This is a dermoscopic photograph of a skin lesion. A female subject in their 60s: 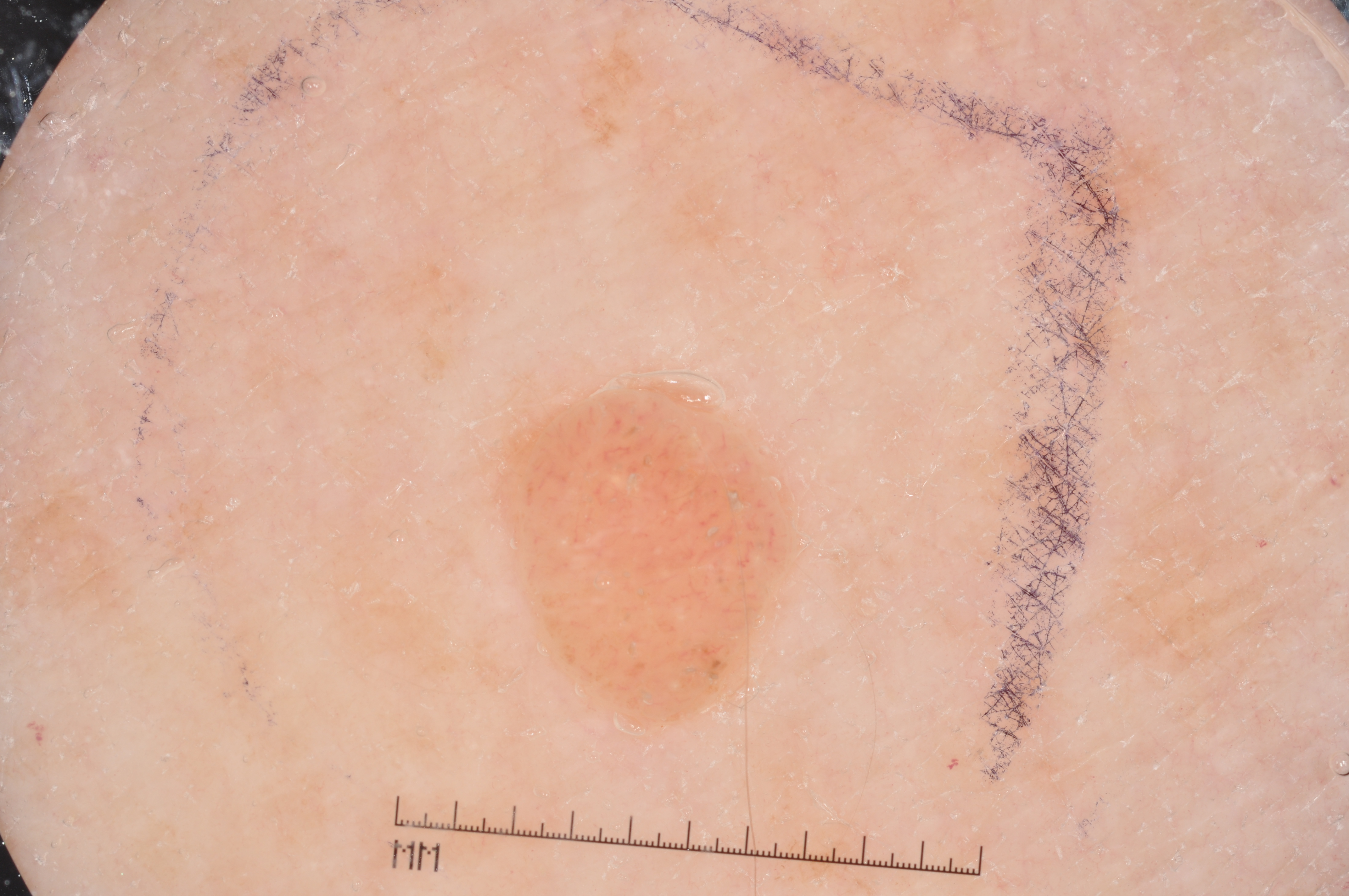The lesion occupies roughly 6% of the field. With coordinates (x1, y1, x2, y2), lesion location: (495, 385, 790, 714). On dermoscopy, the lesion shows milia-like cysts. Clinically diagnosed as a melanocytic nevus, a benign skin lesion.